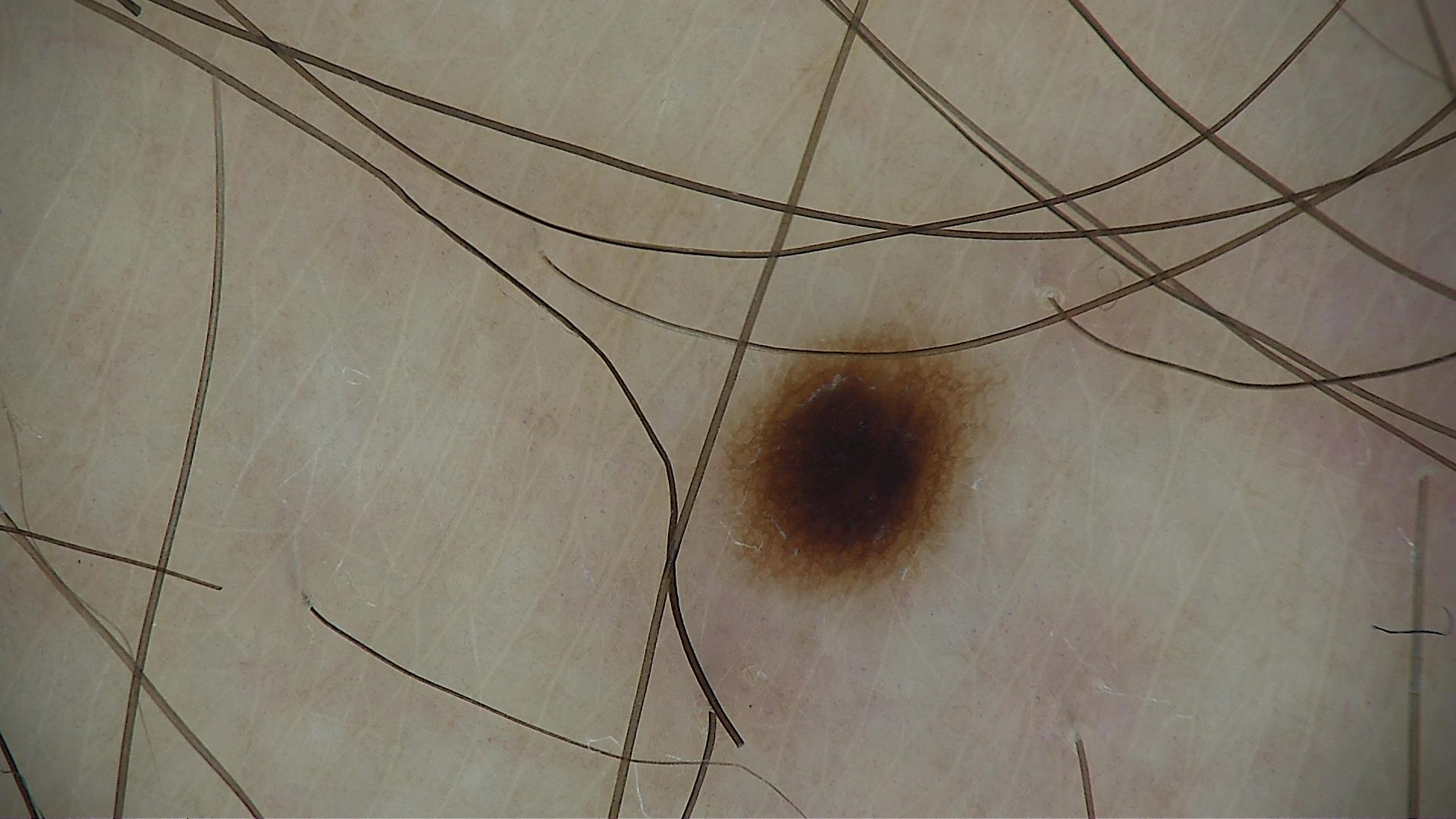| key | value |
|---|---|
| class | dysplastic junctional nevus (expert consensus) |